The affected area is the head or neck, leg and arm · symptoms reported: itching · the patient considered this a rash · texture is reported as raised or bumpy · male patient, age 18–29 · the photograph is a close-up of the affected area · present for about one day.
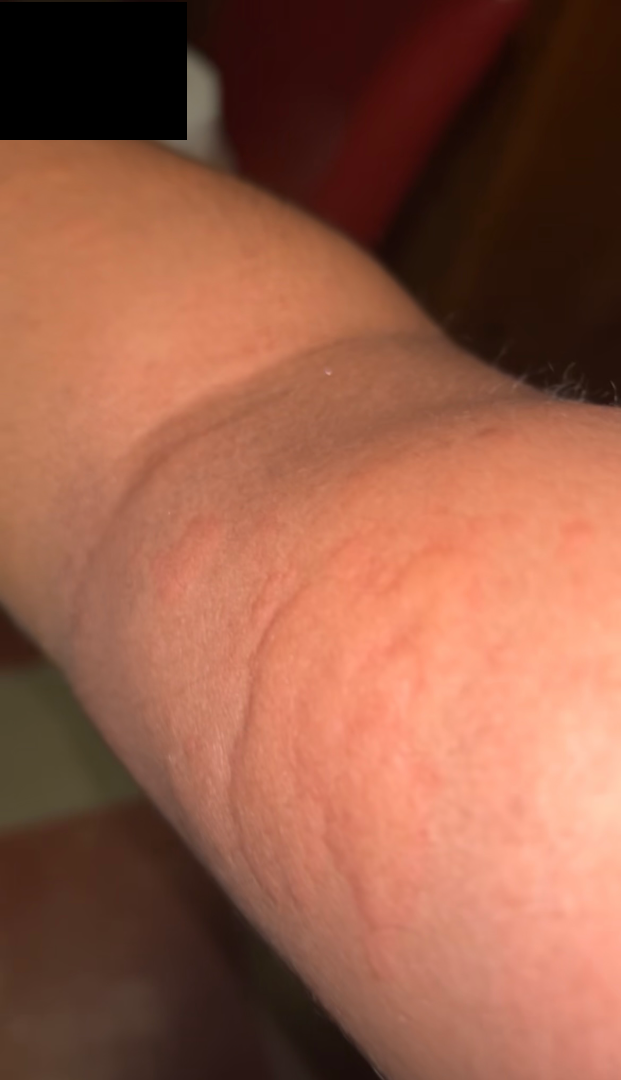Q: What is the dermatologist's impression?
A: Urticaria (100%)